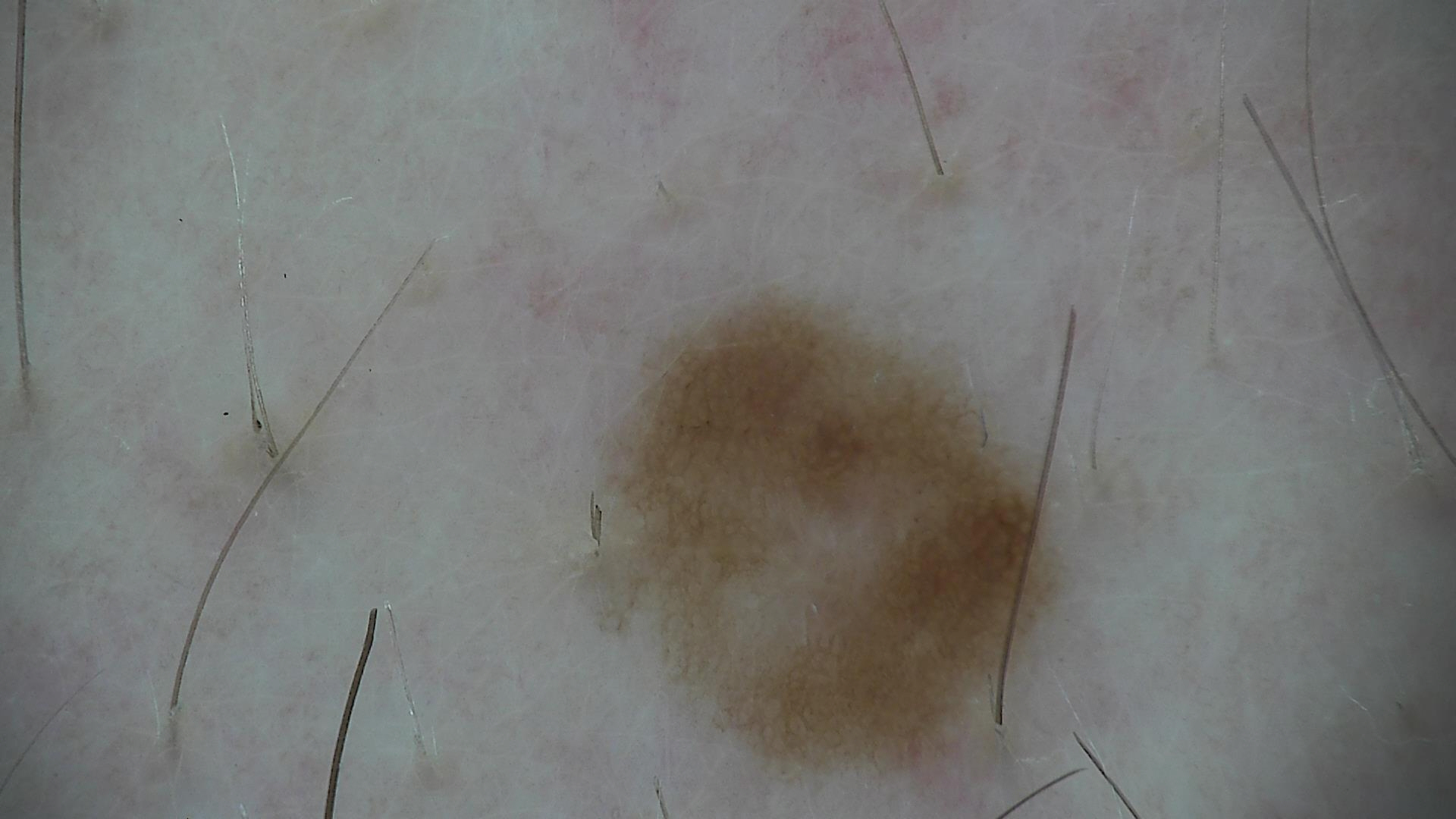Conclusion: Consistent with a dysplastic junctional nevus.